Female subject, age 18–29 · a close-up photograph · located on the arm, top or side of the foot, leg and front of the torso — 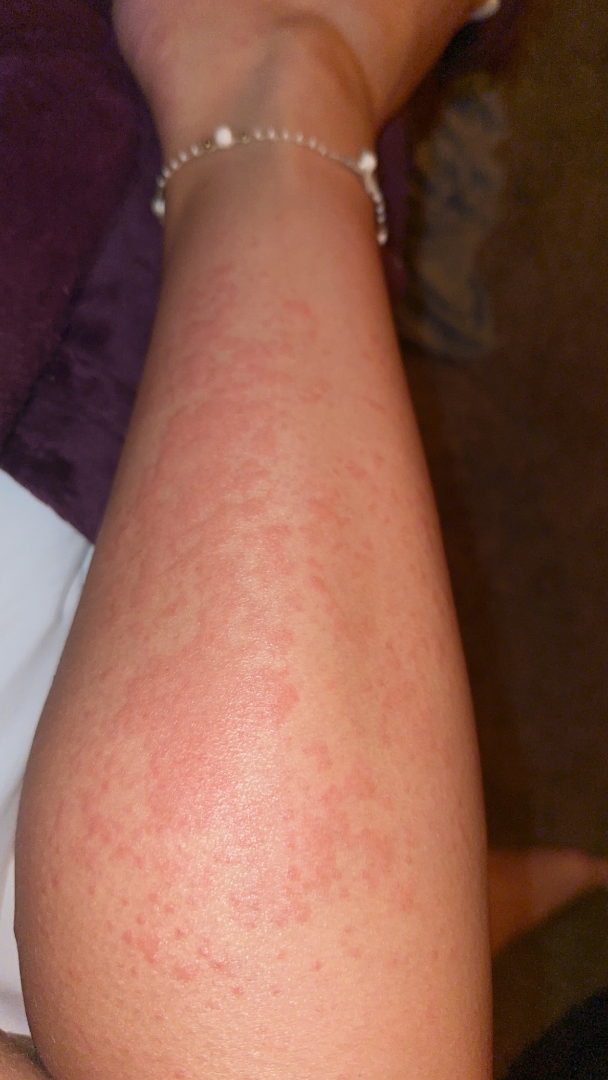systemic_symptoms:
  - fatigue
  - shortness of breath
skin_tone:
  fitzpatrick: IV
  monk_skin_tone:
    - 3
    - 5
differential:
  leading:
    - Allergic Contact Dermatitis
  considered:
    - Urticaria
  unlikely:
    - Eczema